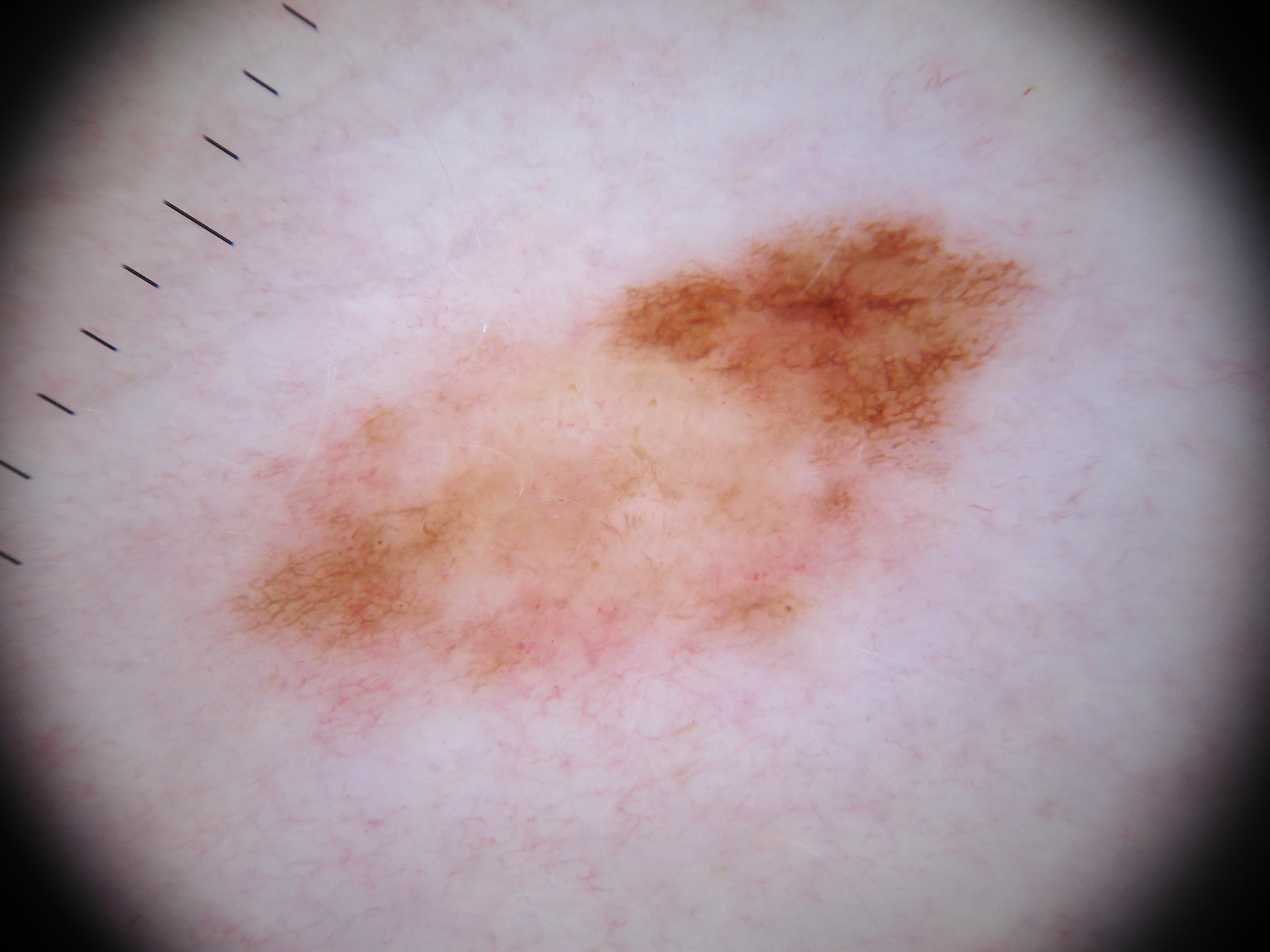| feature | finding |
|---|---|
| imaging | dermatoscopic image of a skin lesion |
| lesion location | x1=227, y1=207, x2=1059, y2=743 |
| dermoscopic findings | pigment network |
| diagnosis | a melanocytic nevus, a benign skin lesion |